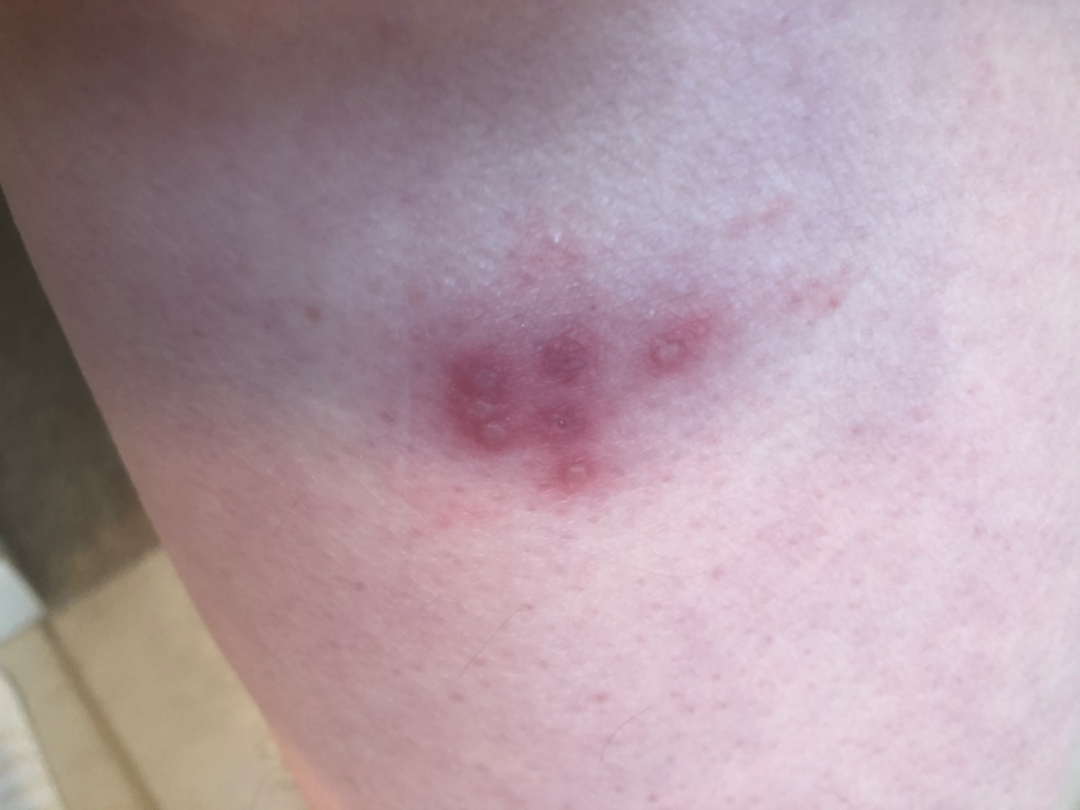image framing = close-up
location = leg
duration = less than one week
surface texture = raised or bumpy and fluid-filled
dermatologist impression = most likely Herpes Simplex; also on the differential is Herpes Zoster